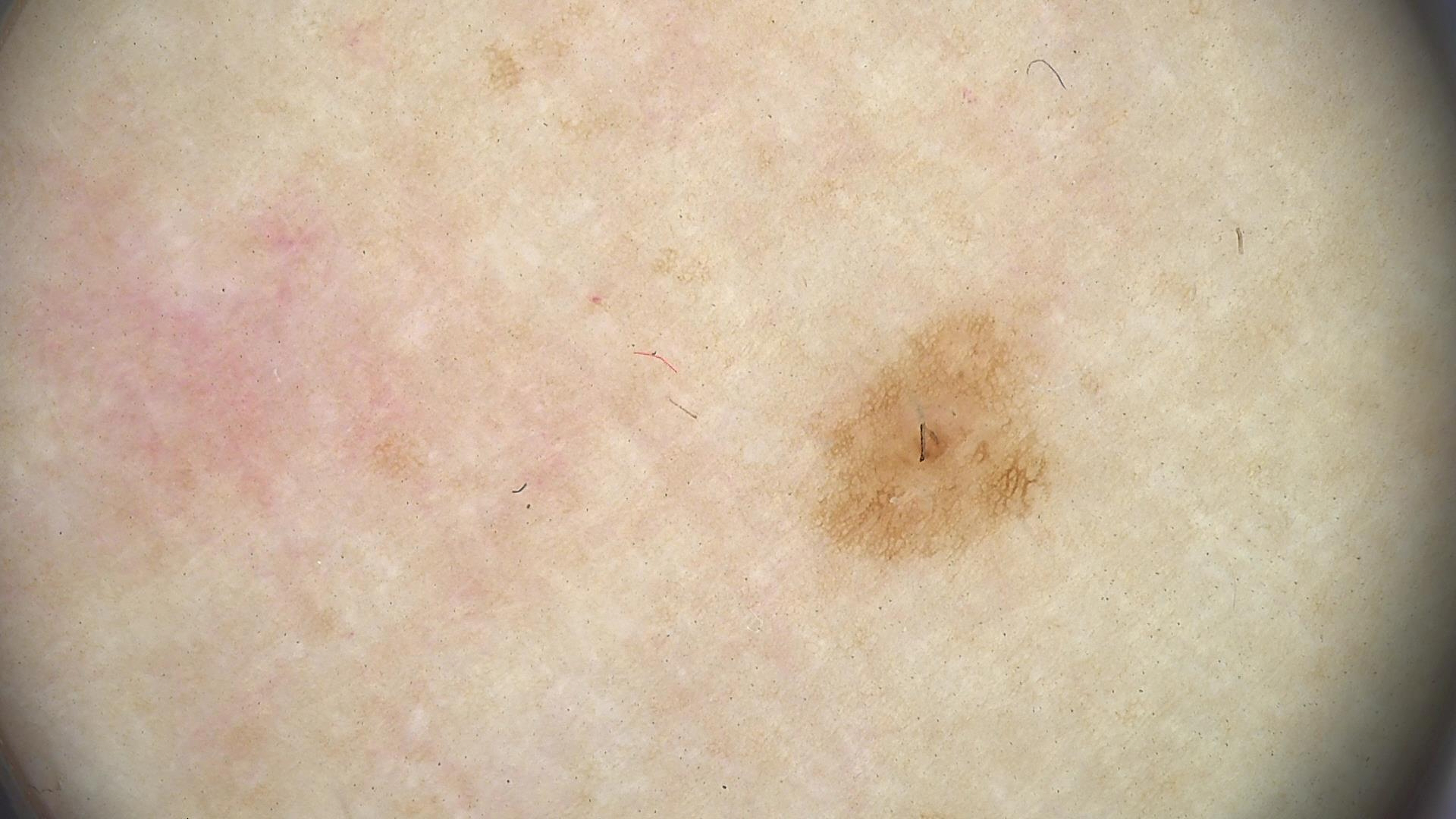diagnosis — junctional nevus (expert consensus).